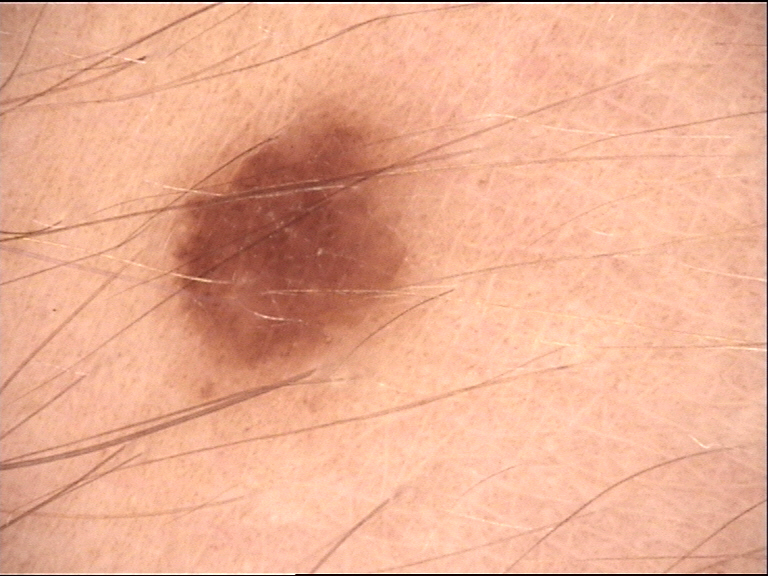Labeled as a junctional nevus.